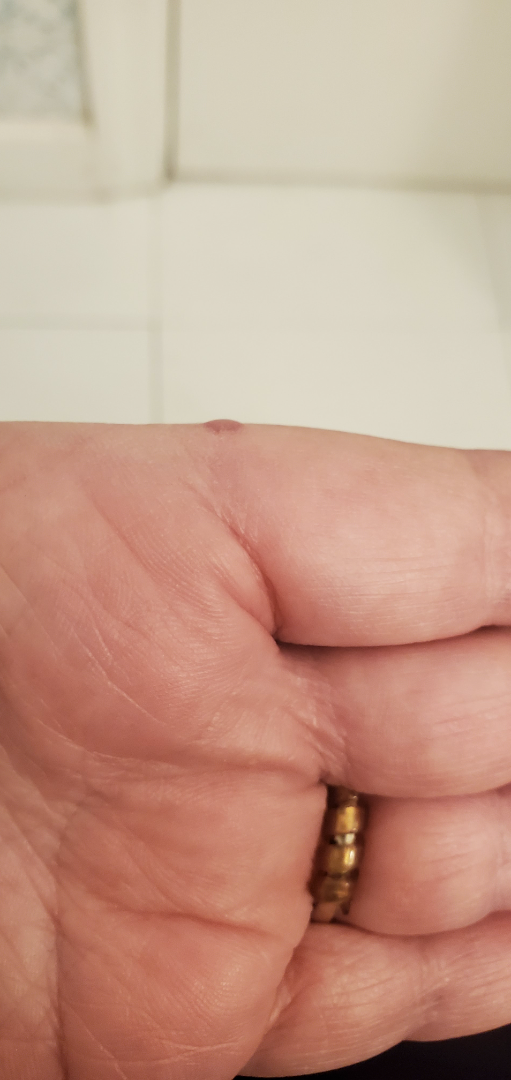Notes:
- assessment · could not be assessed
- contributor · female, age 50–59
- shot type · at an angle
- site · palm